Skin tone: Fitzpatrick skin type IV; the lesion involves the leg; reported duration is about one day; the photo was captured at an angle; the patient considered this a rash; reported lesion symptoms include itching:
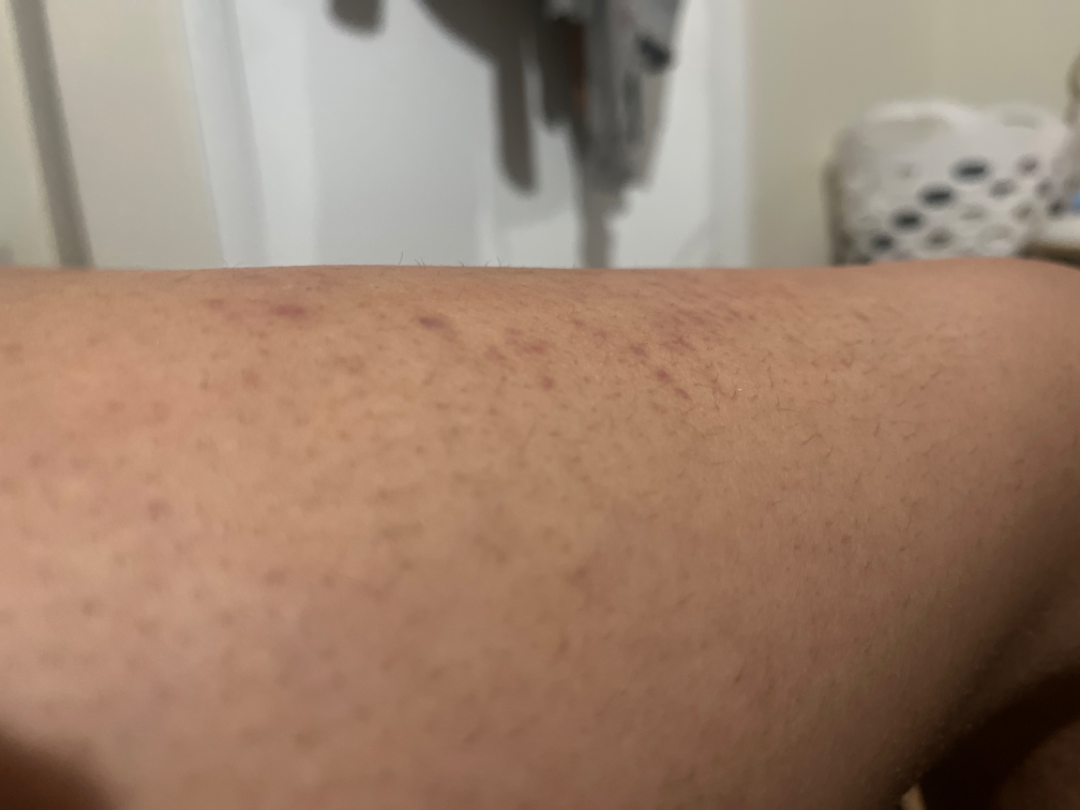Q: What was the assessment?
A: not assessable